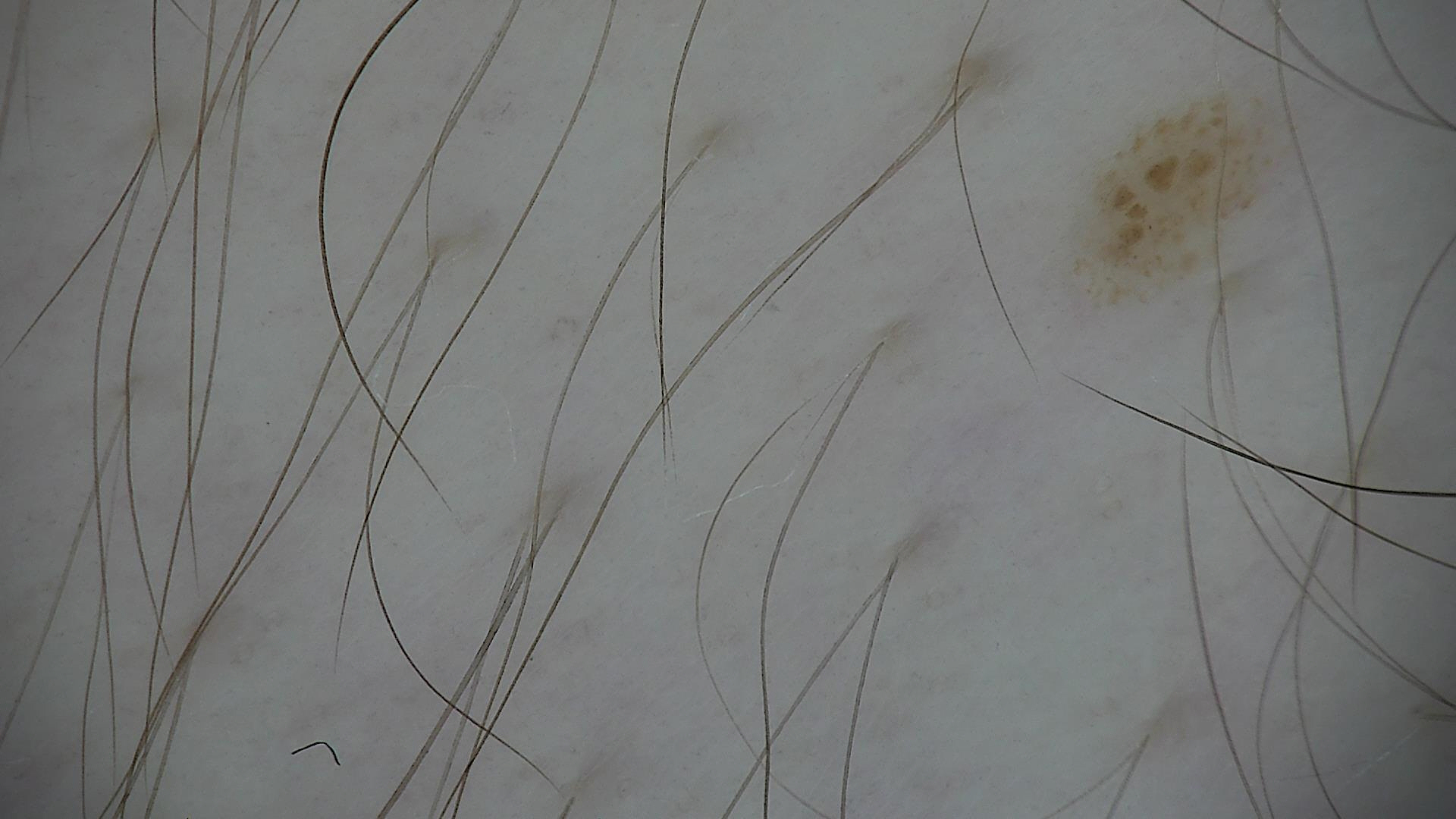{
  "diagnosis": {
    "name": "dysplastic junctional nevus",
    "code": "jd",
    "malignancy": "benign",
    "super_class": "melanocytic",
    "confirmation": "expert consensus"
  }
}